A male patient, aged approximately 65. Dermoscopy of a skin lesion:
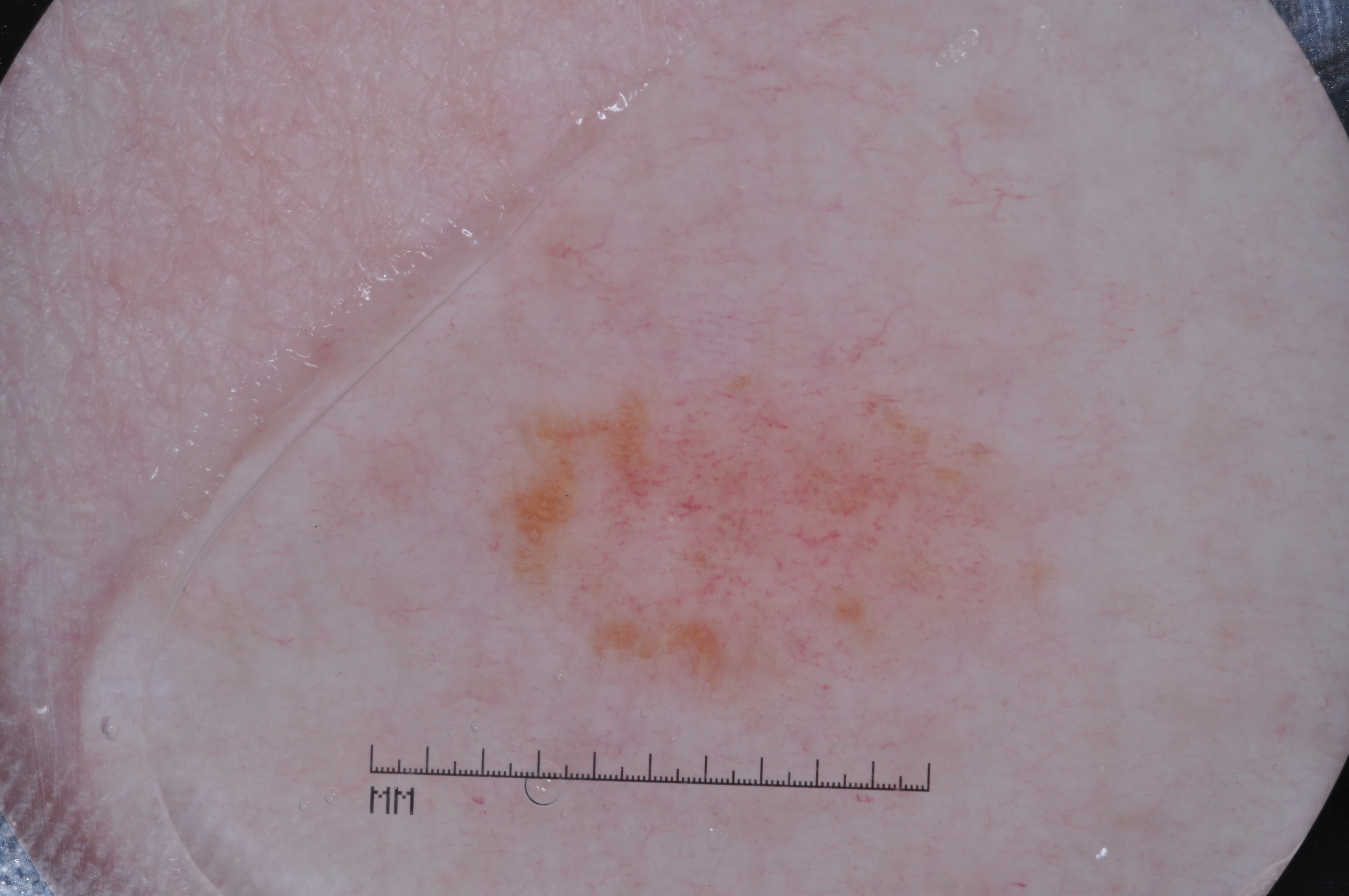{"dermoscopic_features": {"present": ["pigment network"], "absent": ["milia-like cysts", "streaks", "negative network"]}, "lesion_location": {"bbox_xyxy": [489, 356, 1074, 714]}, "diagnosis": {"name": "melanocytic nevus", "malignancy": "benign", "lineage": "melanocytic", "provenance": "clinical"}}